This is a close-up image, present for about one day, self-reported Fitzpatrick skin type V, self-categorized by the patient as skin that appeared healthy to them, the patient reports the lesion is raised or bumpy: 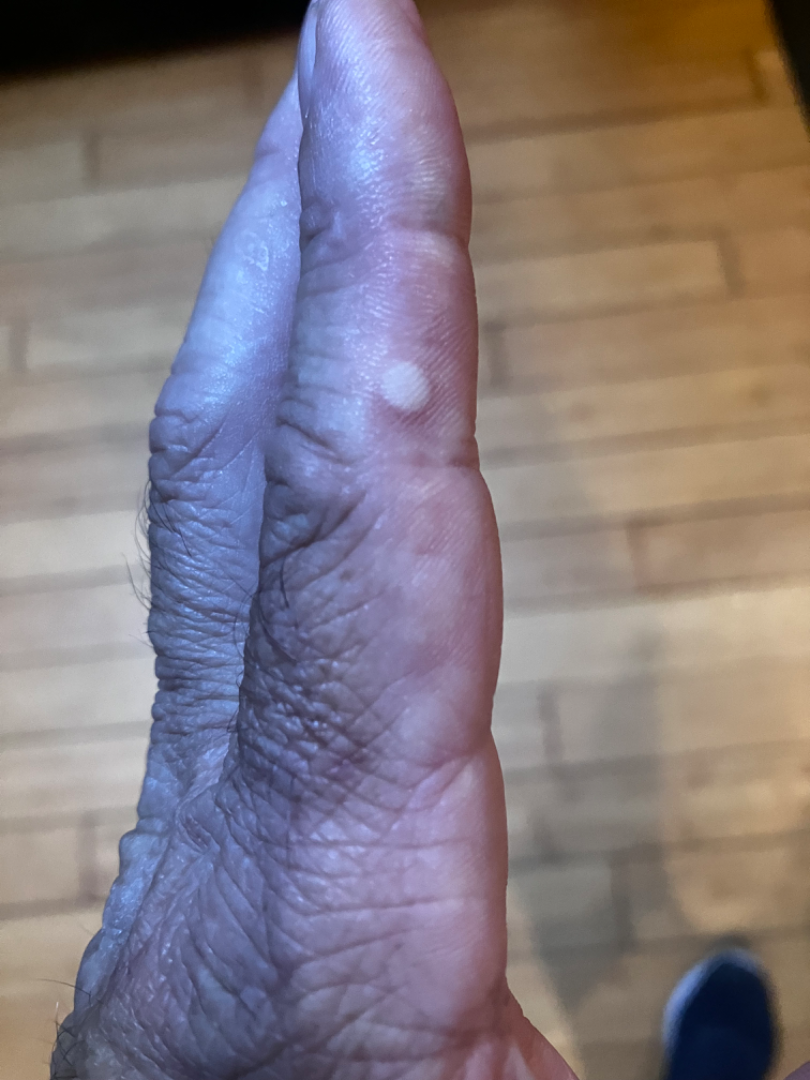Q: Could the case be diagnosed?
A: not assessable